A dermoscopic close-up of a skin lesion.
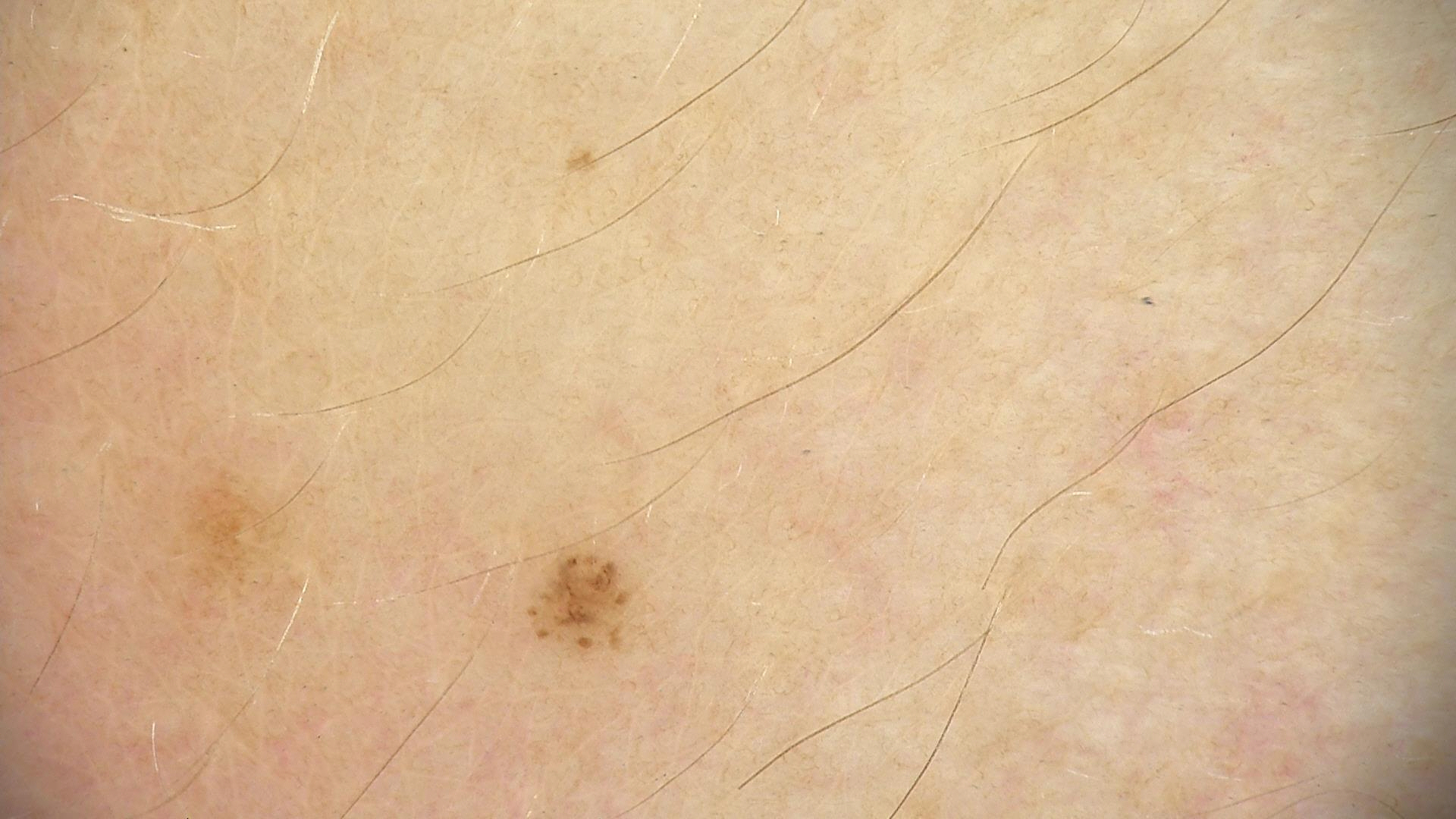Consistent with a dysplastic junctional nevus.